Collected as part of a research study, without a referral diagnosis. A macroscopic clinical photograph of a skin lesion. A female subject age 15: 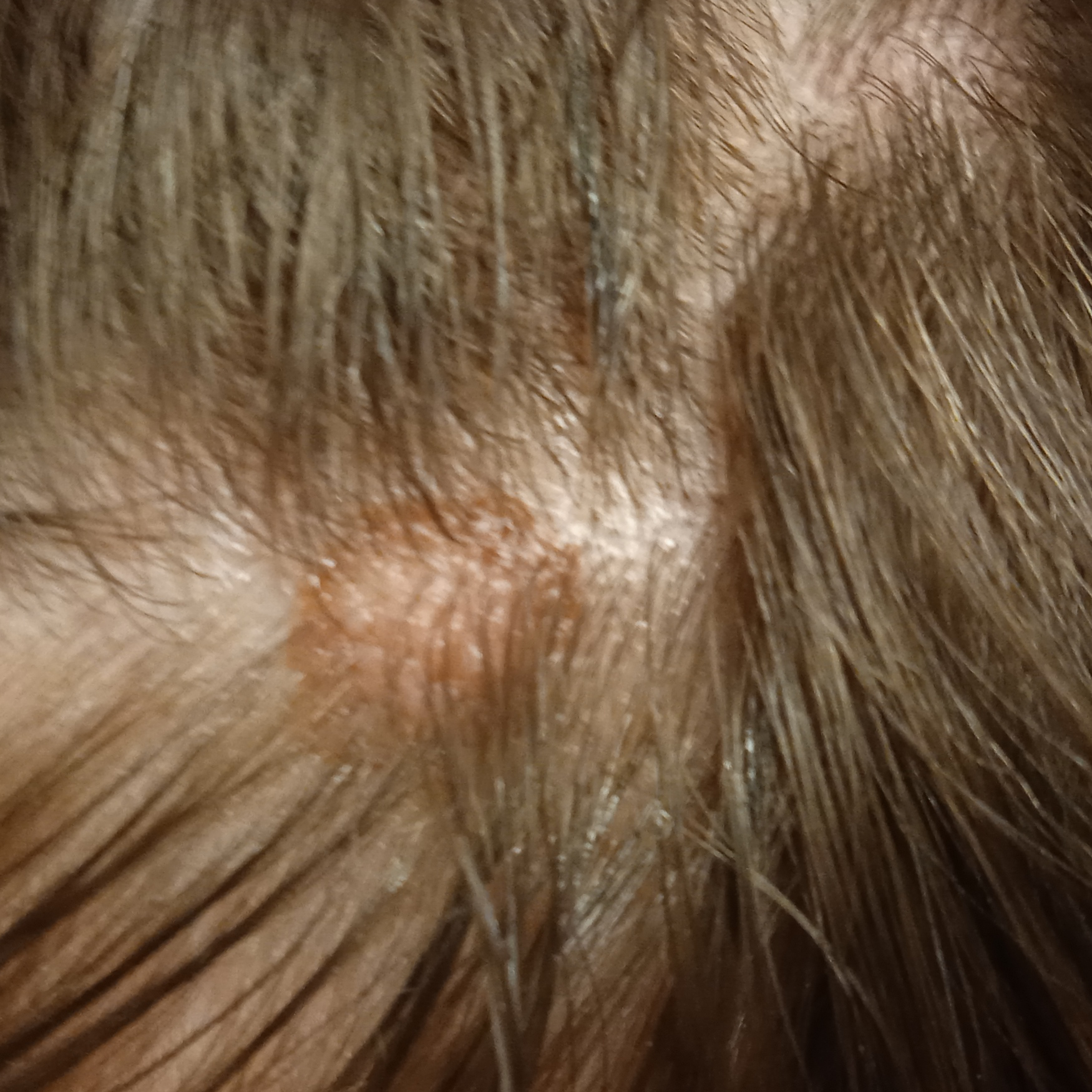| feature | finding |
|---|---|
| location | the head |
| lesion size | 9.1 mm |
| diagnosis | melanocytic nevus (dermatologist consensus) |